The patient says their skin reddens painfully with sun exposure; imaged for a research study, with no referral diagnosis recorded; dermoscopy of a skin lesion; a male subject age 89:
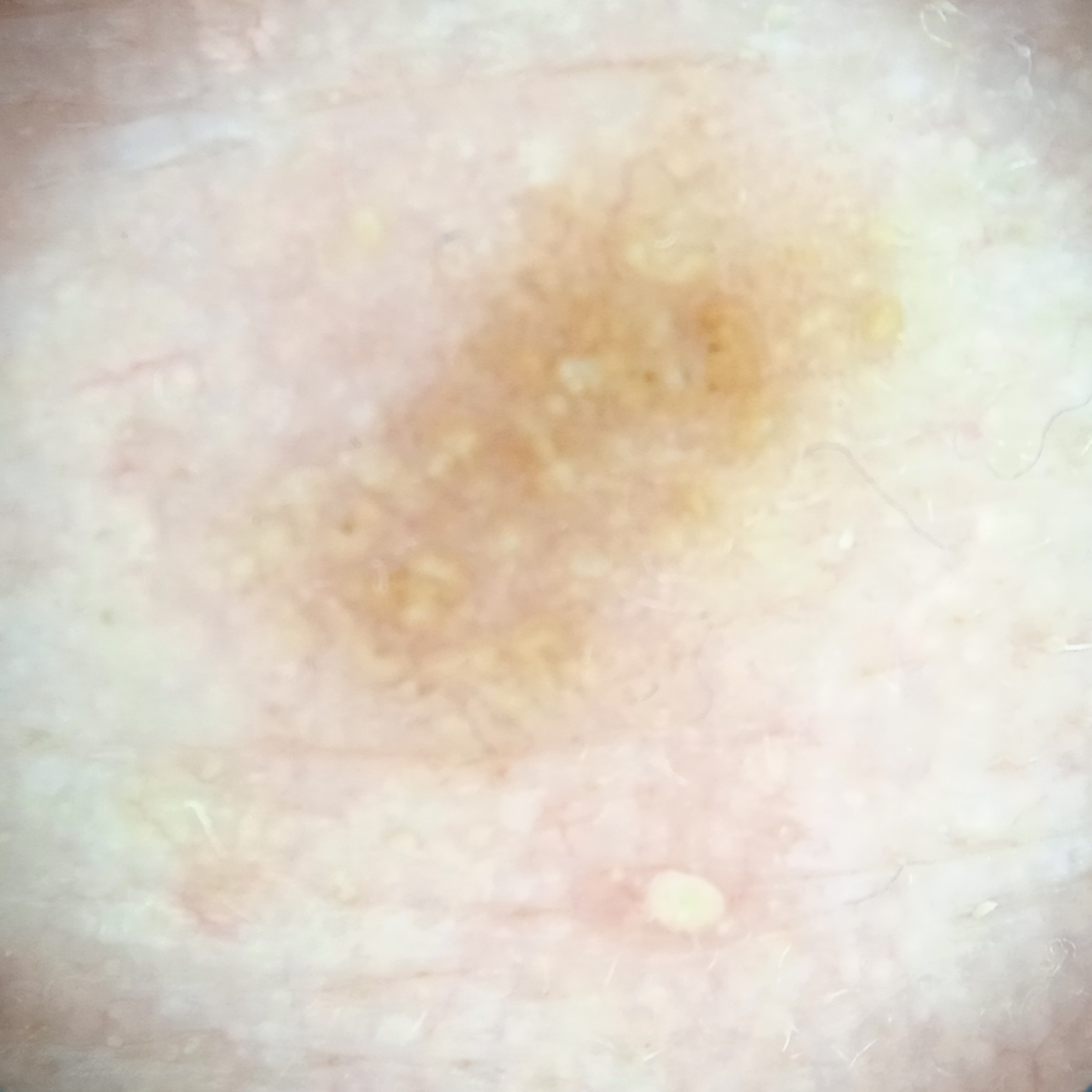Clinical context:
The lesion involves the face. The lesion measures approximately 6.4 mm.
Assessment:
The diagnostic impression was an actinic keratosis.